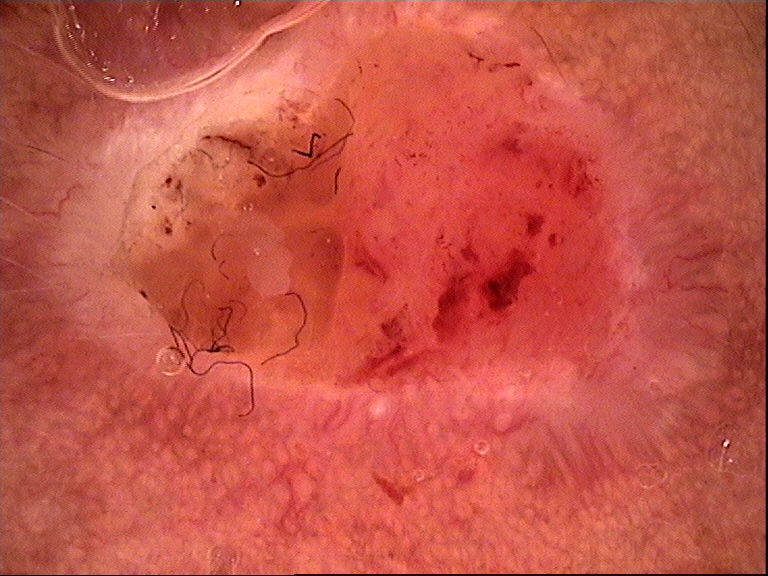Biopsy-confirmed as a squamous cell carcinoma.